The photo was captured at a distance:
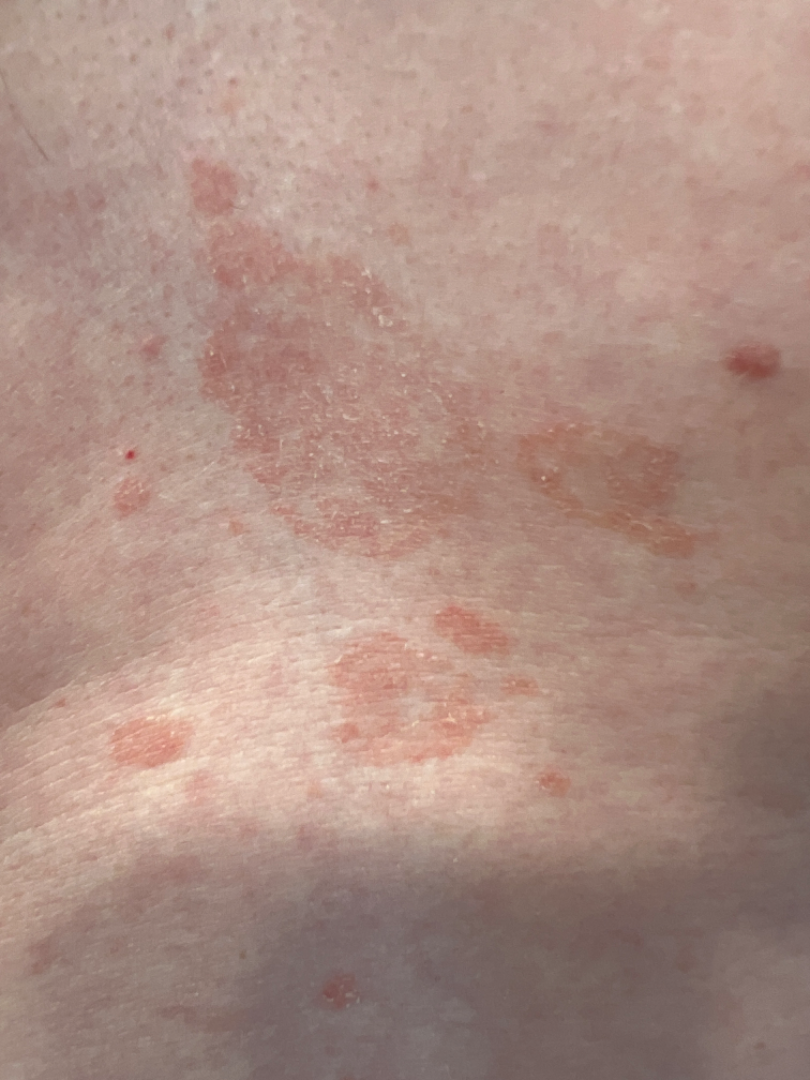No differential diagnosis could be assigned on photographic review.